A dermoscopic photograph of a skin lesion.
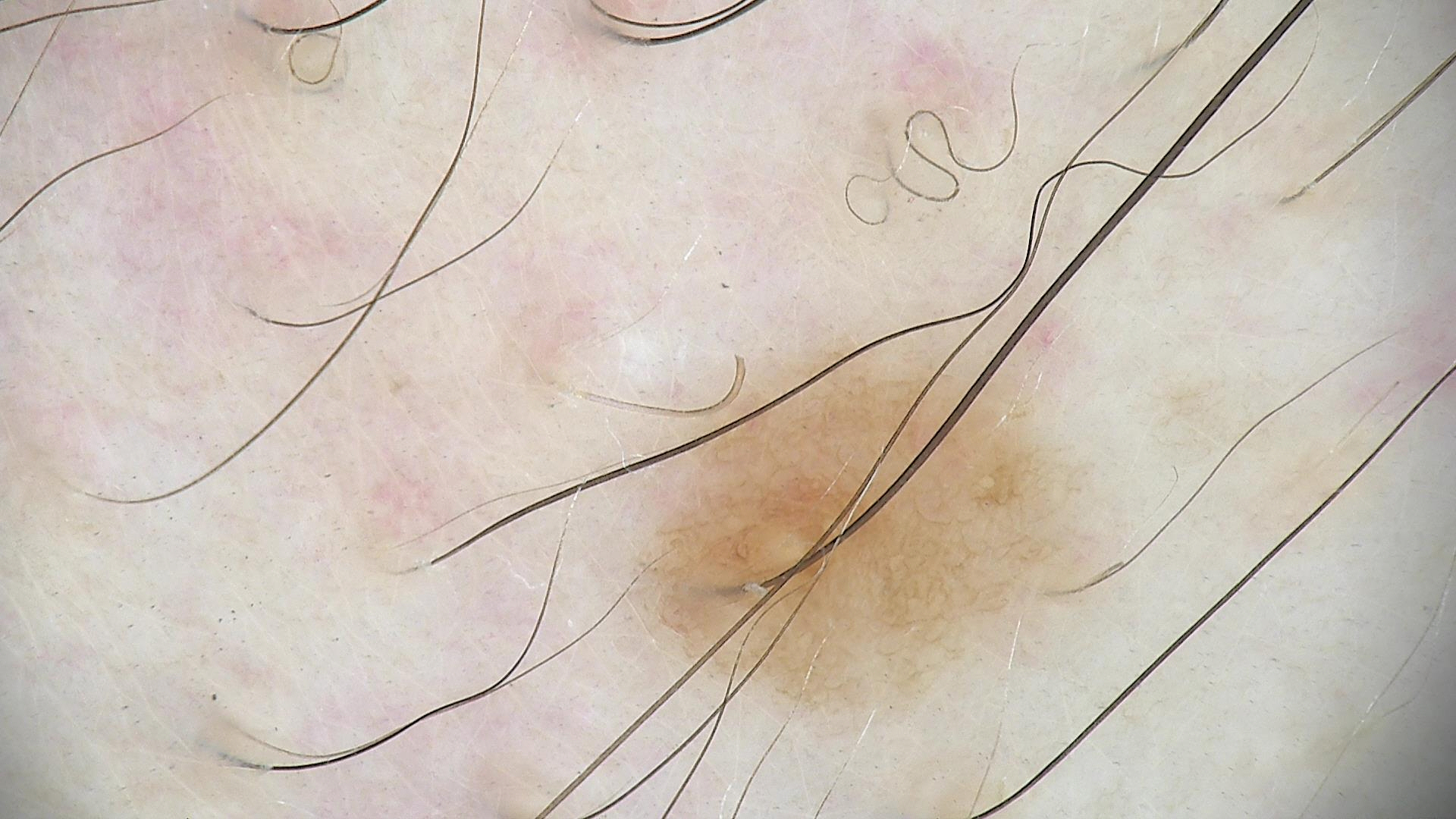Q: What was the diagnostic impression?
A: dysplastic junctional nevus (expert consensus)